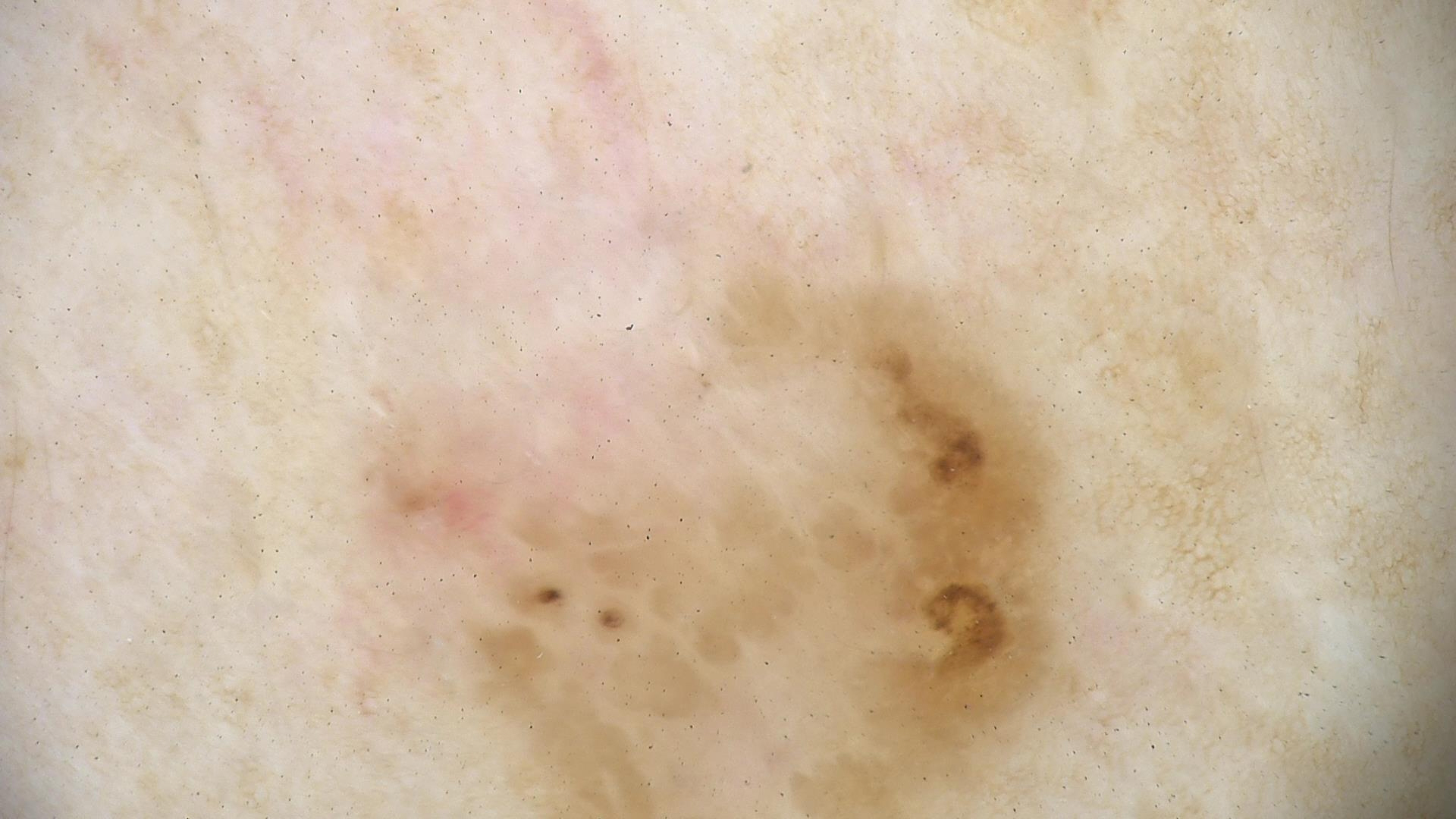image: dermoscopy, diagnostic label: seborrheic keratosis (expert consensus).